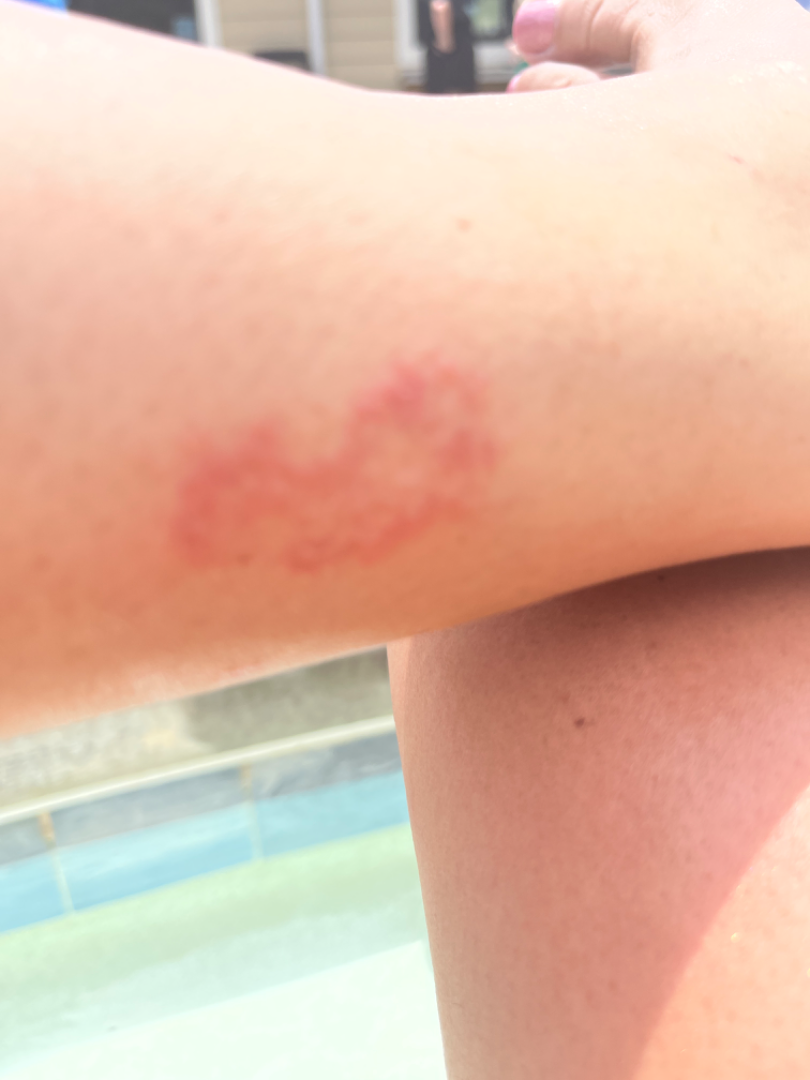  assessment: unable to determine
  shot_type: close-up